Close-up view; the affected area is the arm.
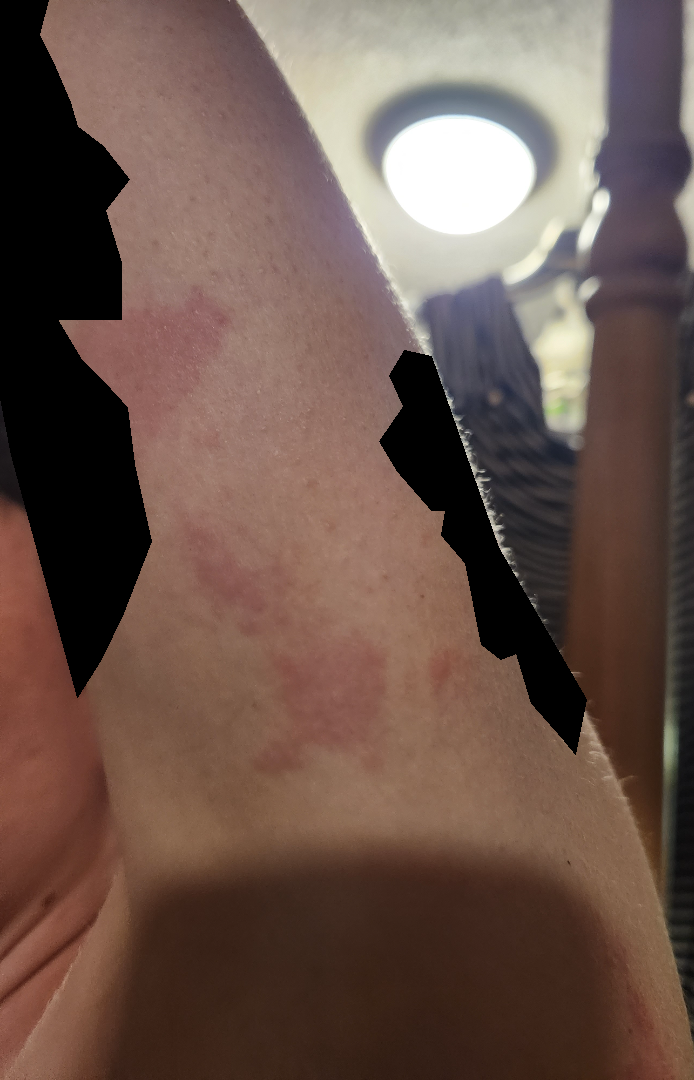Notes:
• other reported symptoms · none reported
• self-categorized as · a rash
• patient-reported symptoms · itching
• dermatologist impression · Allergic Contact Dermatitis and Irritant Contact Dermatitis were each considered, in no particular order